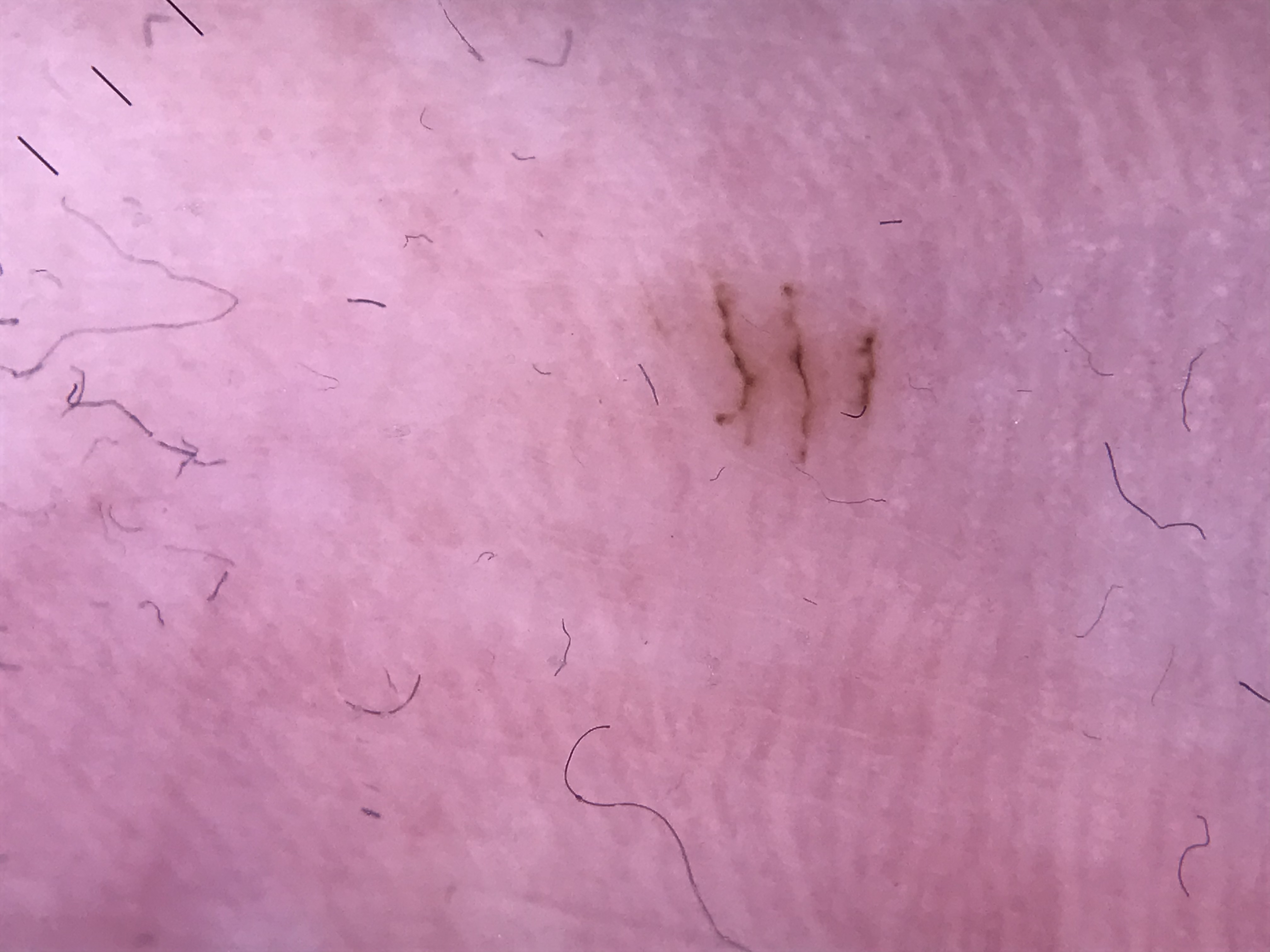This is a banal lesion.
Classified as an acral junctional nevus.